A dermoscopic photograph of a skin lesion.
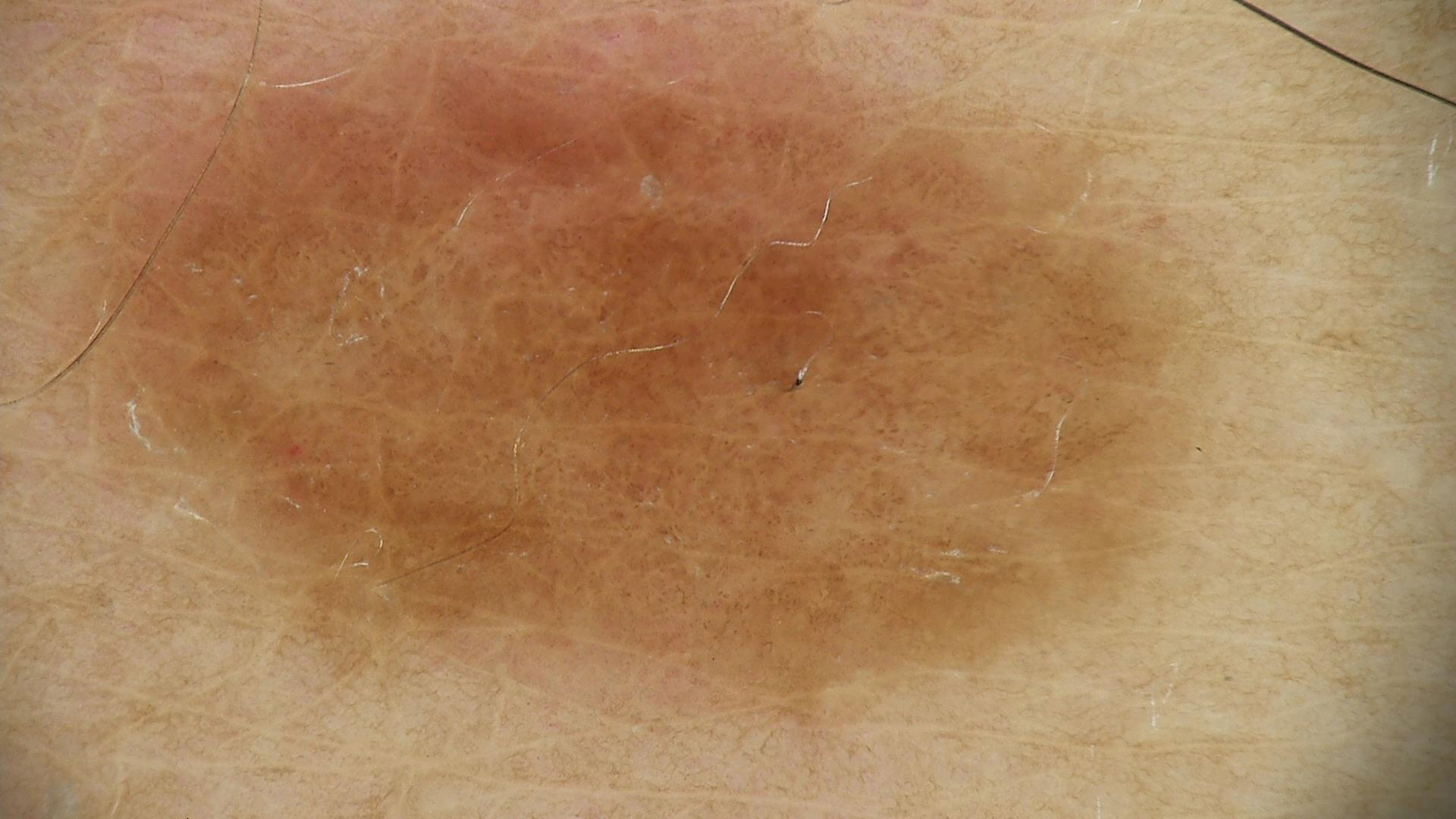Impression: The diagnostic label was a dysplastic junctional nevus.